A close-up photograph: 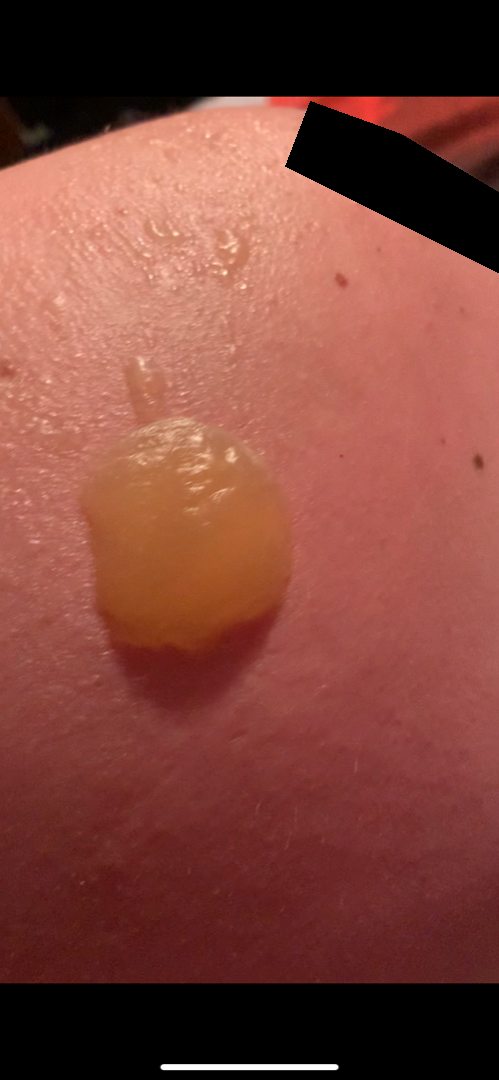Q: What was the assessment?
A: not assessable